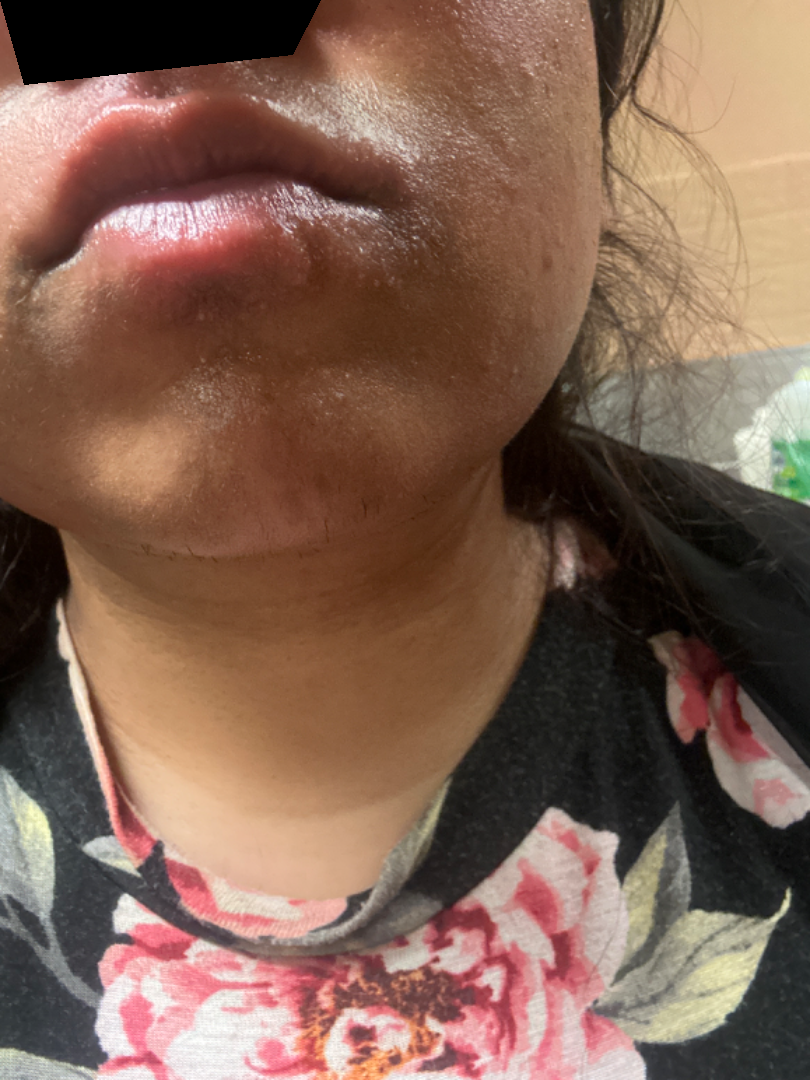Impression: The case was indeterminate on photographic review. History: The contributor is 18–29, female. Close-up view.